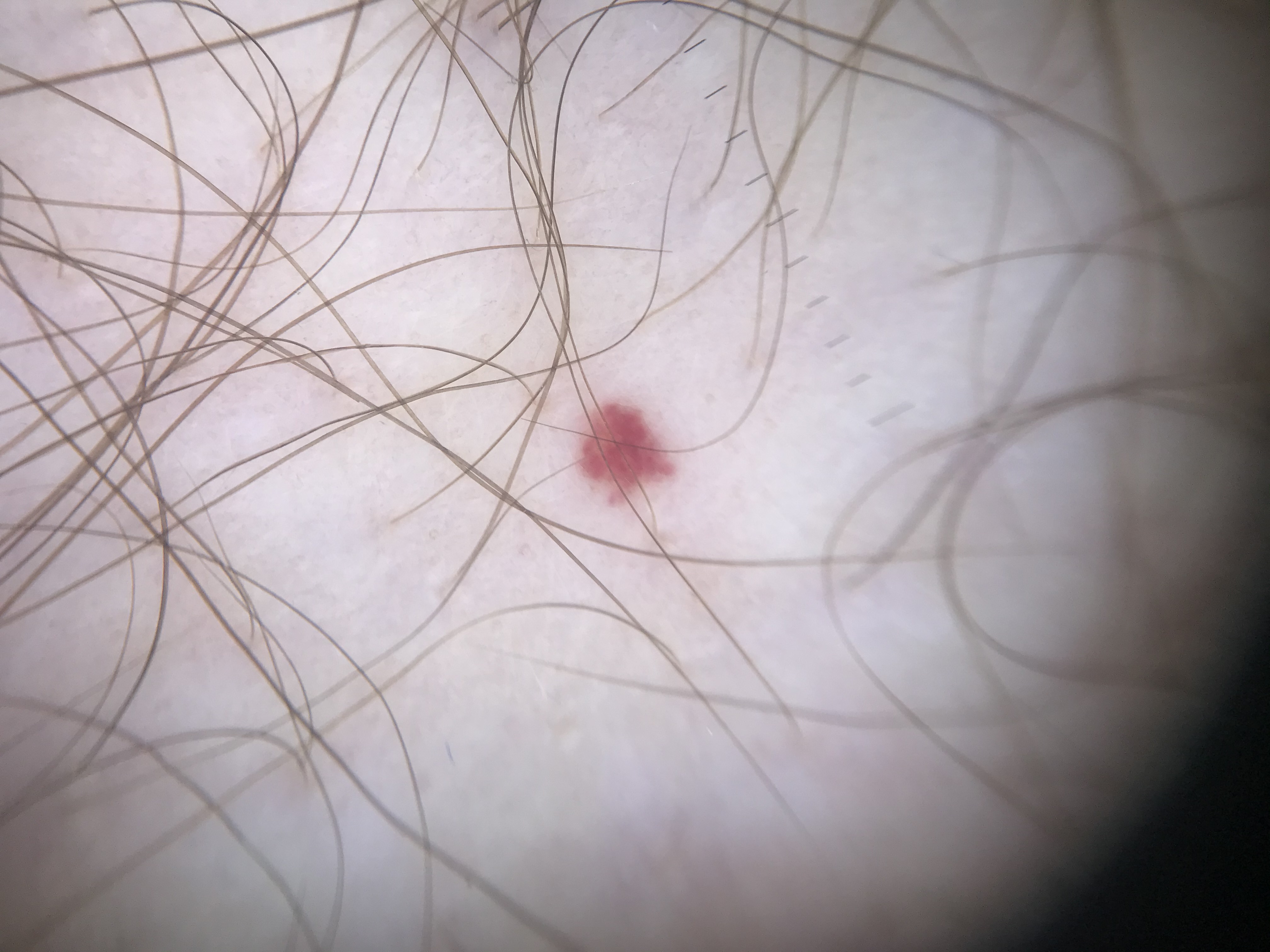Impression: Labeled as a hemangioma.